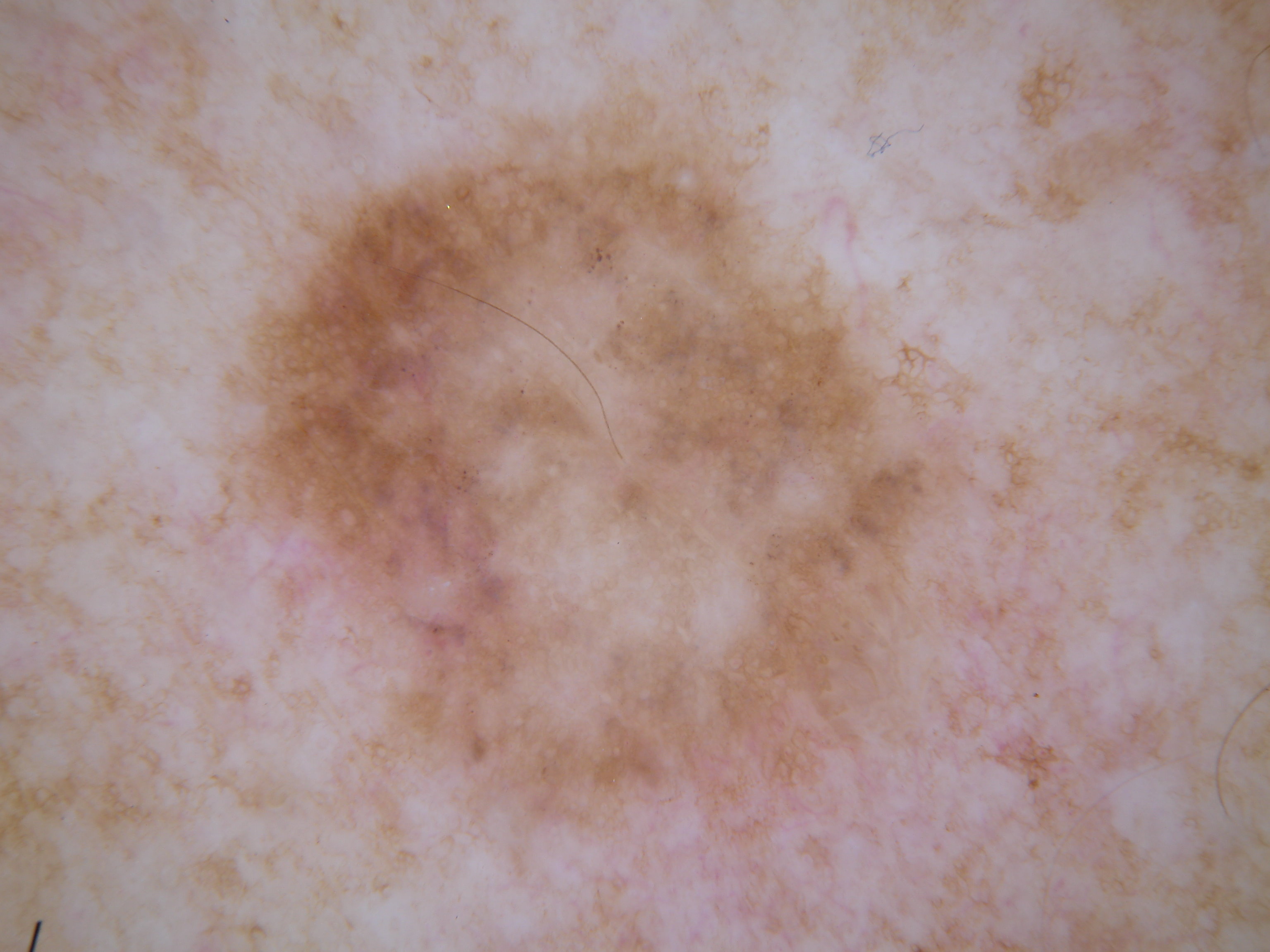Q: What kind of image is this?
A: dermatoscopic image of a skin lesion
Q: Where is the lesion in the image?
A: <box>206, 107, 997, 887</box>
Q: What is this lesion?
A: a melanocytic nevus